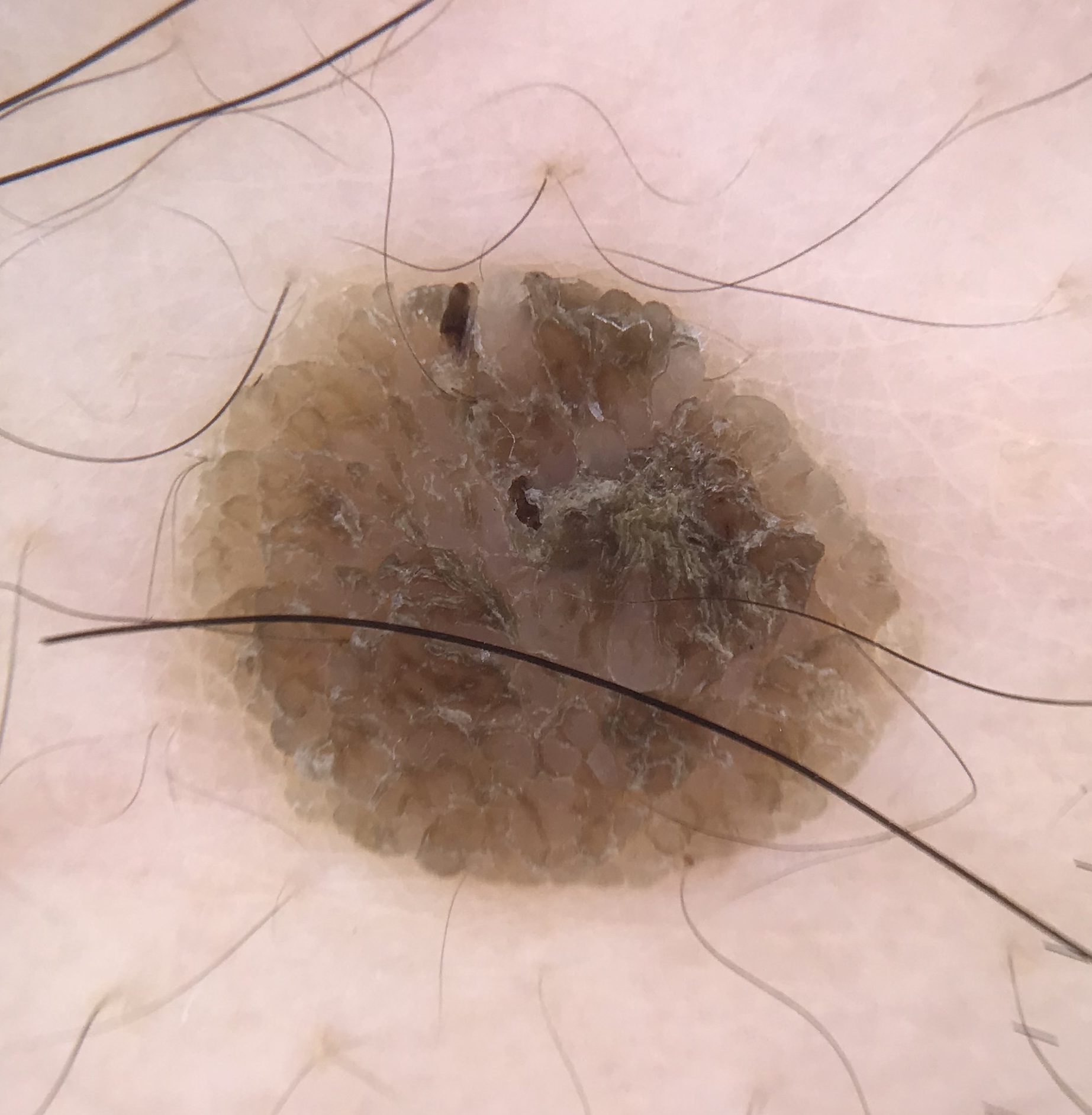Dermoscopy of a skin lesion. The architecture is that of a keratinocytic lesion. Classified as a seborrheic keratosis.